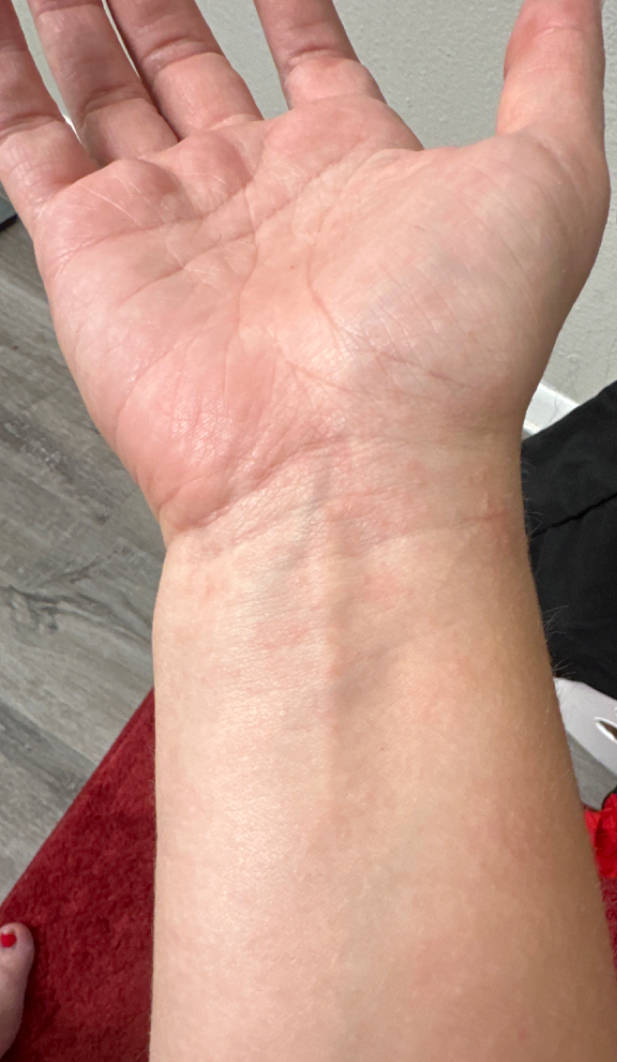assessment — could not be assessed